A dermoscopic close-up of a skin lesion:
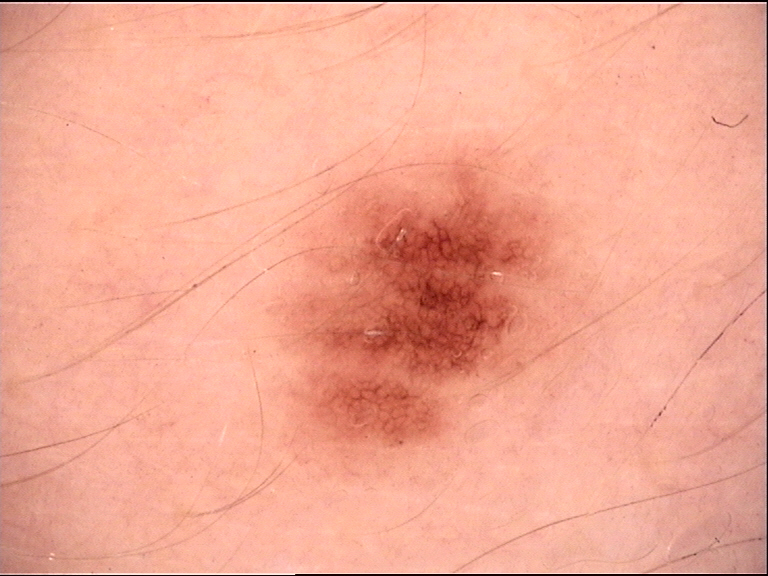The morphology is that of a banal lesion. Consistent with a junctional nevus.